A dermoscopic close-up of a skin lesion: 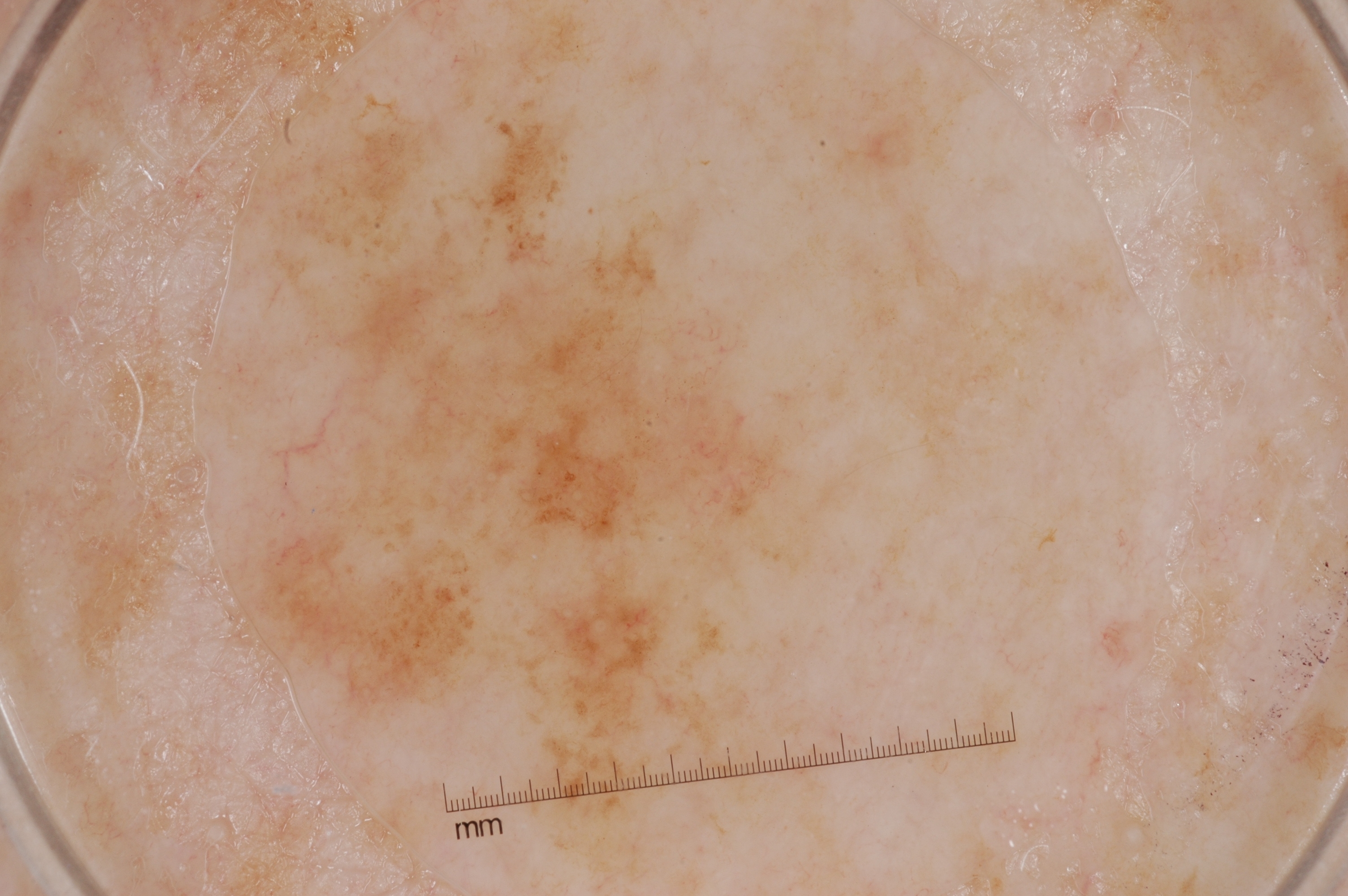location — bbox(149, 2, 817, 872)
diagnostic label — a melanoma